A skin lesion imaged with contact-polarized dermoscopy · a female patient about 55 years old.
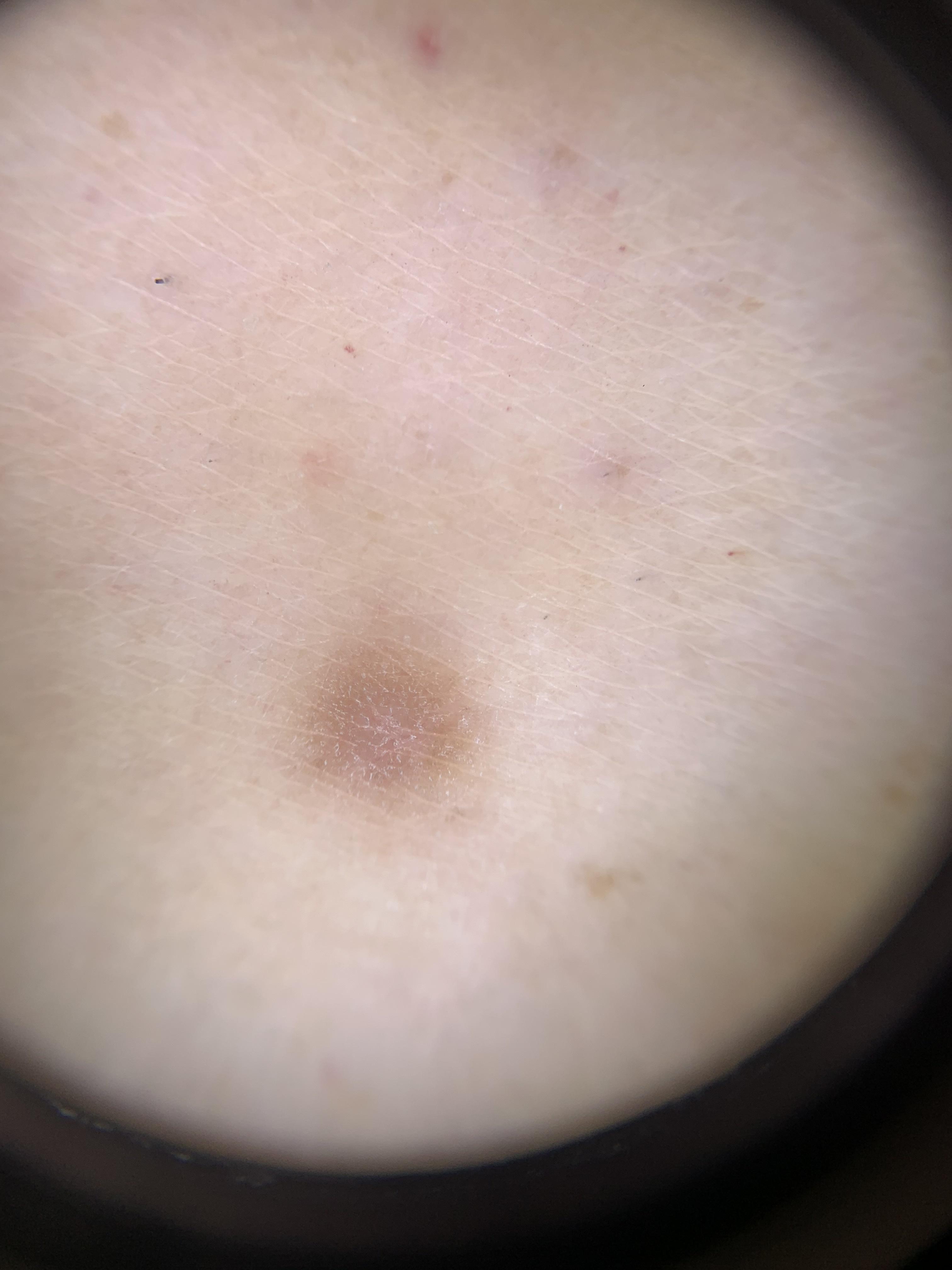Histopathology confirmed a dermatofibroma.